Present for about one day · the patient described the issue as skin that appeared healthy to them · reported lesion symptoms include itching and burning · the affected area is the front of the torso · an image taken at an angle · Fitzpatrick phototype IV; human graders estimated 3 on the MST · the contributor notes the lesion is raised or bumpy · associated systemic symptoms include chills:
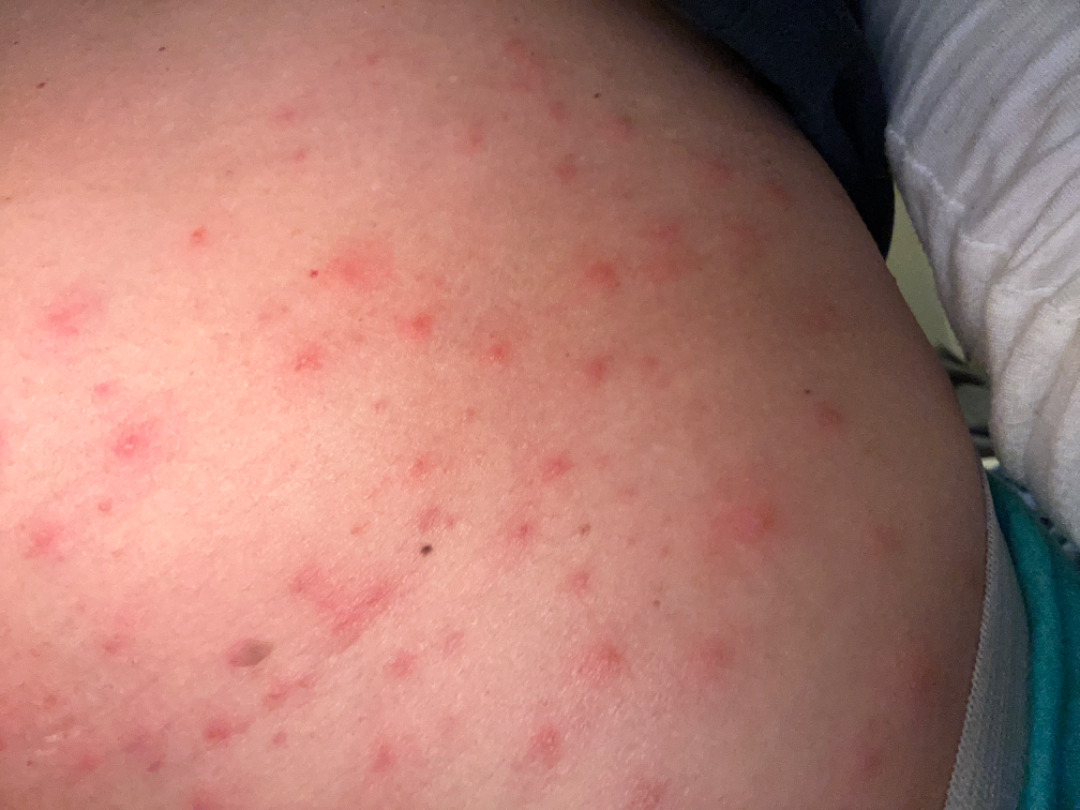On photographic review by a dermatologist, Scabies (weight 0.33); Folliculitis (weight 0.33); Insect Bite (weight 0.33).